The contributor is 40–49, female · a close-up photograph · the lesion involves the arm.
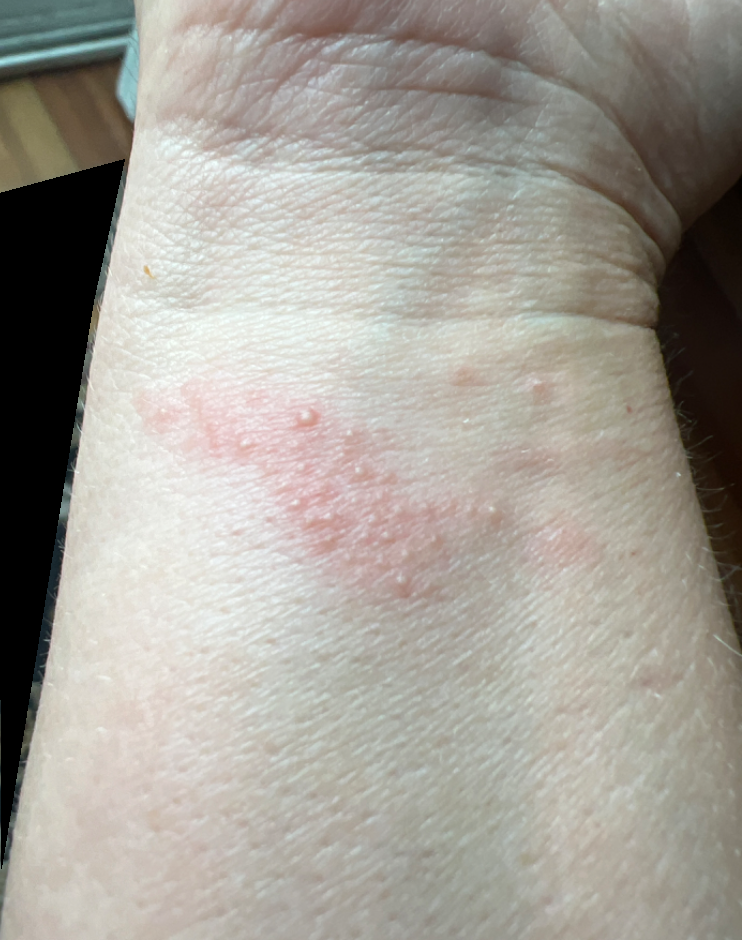{"duration": "about one day", "skin_tone": {"fitzpatrick": "III"}, "patient_category": "a rash", "symptoms": "itching", "texture": "raised or bumpy", "differential": {"leading": ["Allergic Contact Dermatitis"], "considered": ["Herpes Simplex", "Eczema"], "unlikely": ["Lichen nitidus"]}}